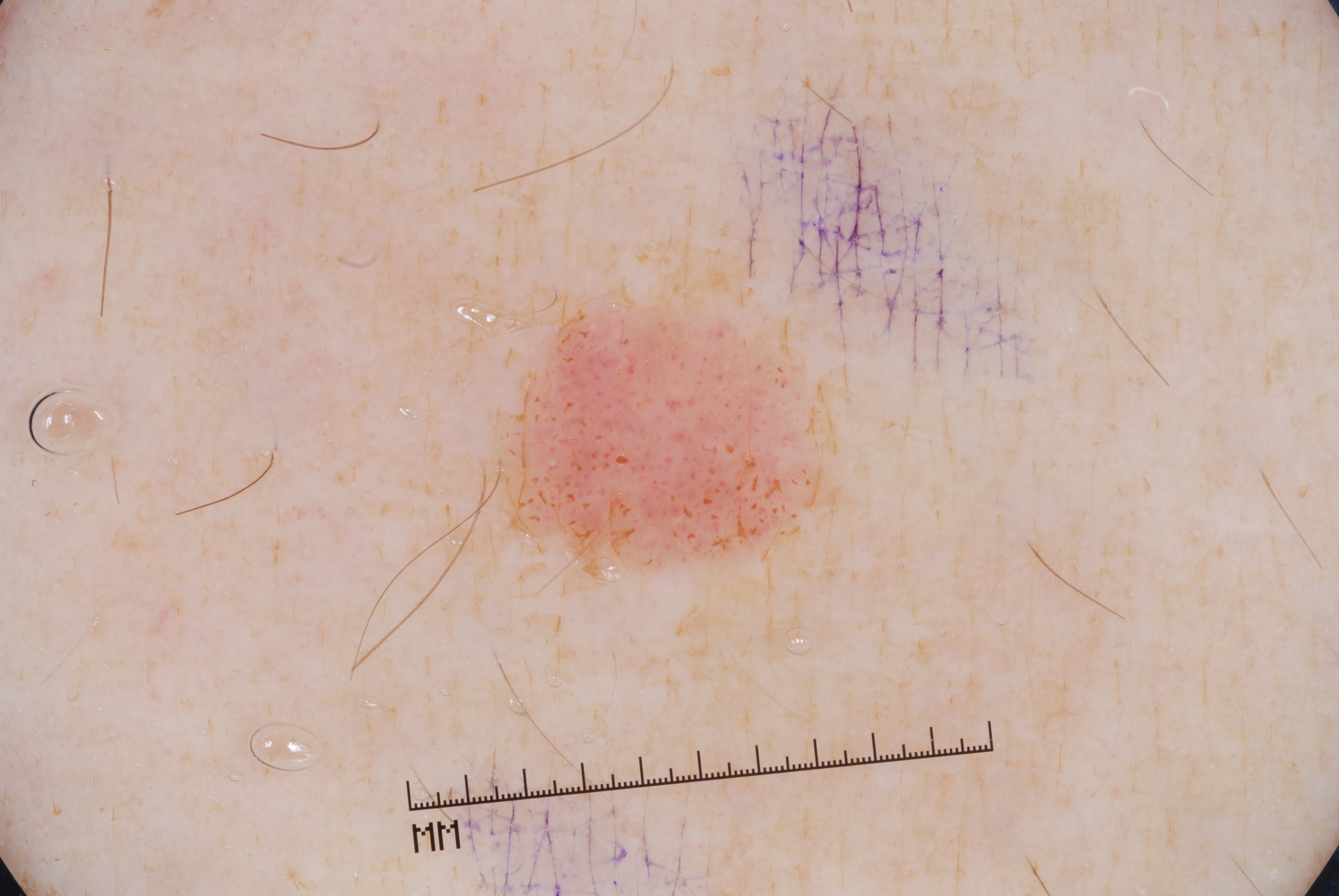Q: What is the imaging modality?
A: dermoscopic image
Q: What are the patient's age and sex?
A: male, in their mid- to late 40s
Q: Where is the lesion in the image?
A: <bbox>481, 301, 837, 574</bbox>
Q: What does dermoscopy show?
A: milia-like cysts
Q: What did the assessment conclude?
A: a melanocytic nevus